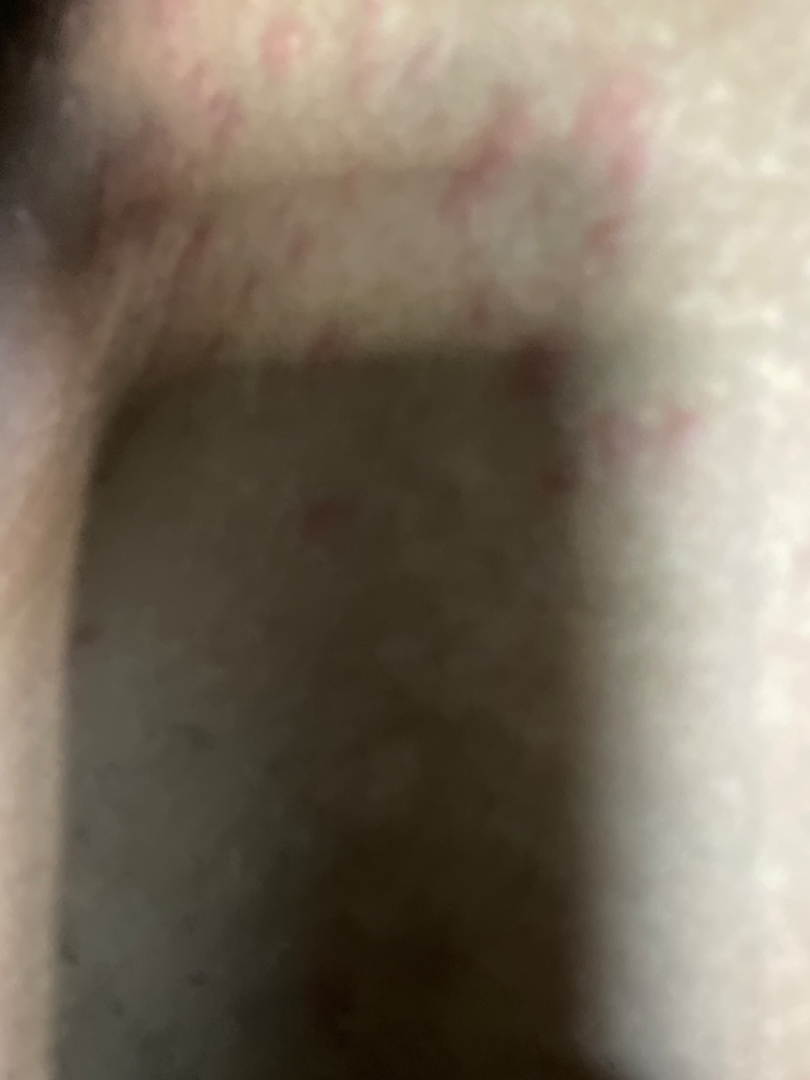<report>
<assessment>indeterminate</assessment>
<shot_type>close-up</shot_type>
<body_site>back of the hand</body_site>
<patient>male, age 40–49</patient>
</report>